The arm is involved. The photograph was taken at a distance: 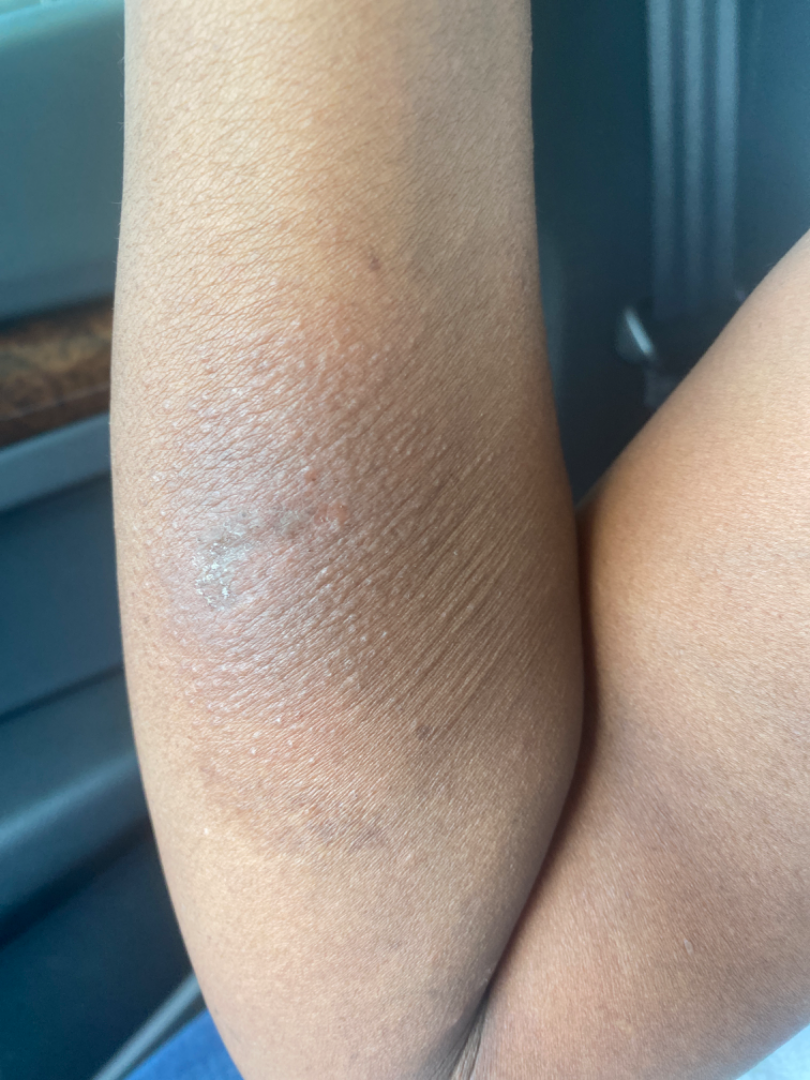assessment — unable to determine.